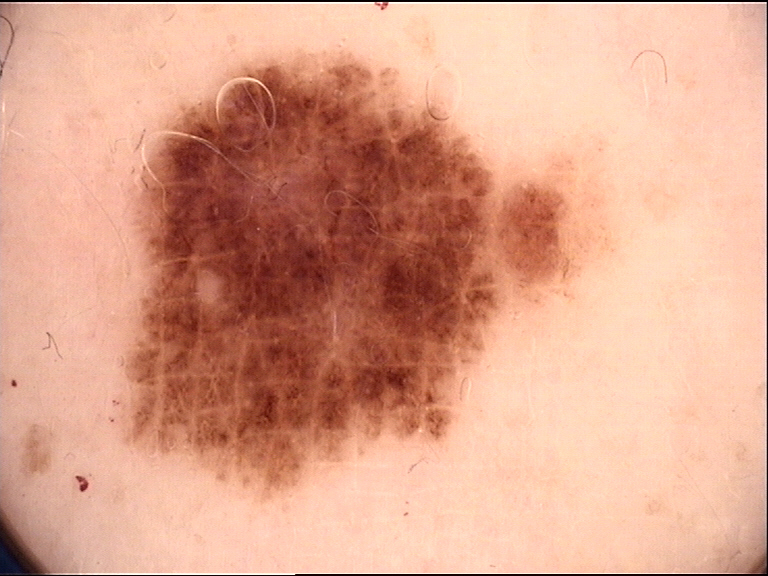Dermoscopy of a skin lesion. Diagnosed as a dysplastic junctional nevus.